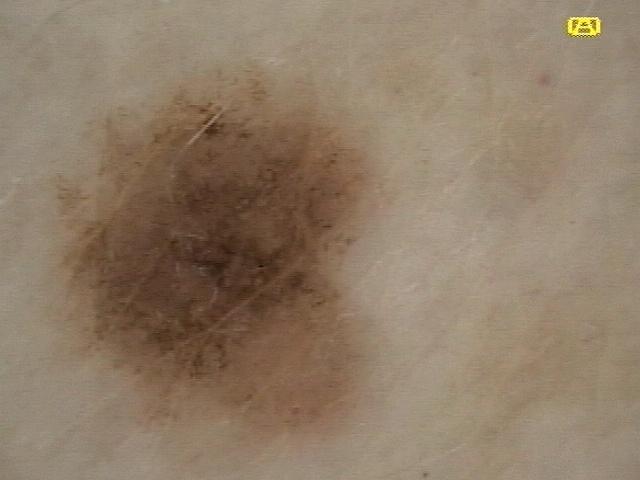A female subject in their mid-60s.
A skin lesion imaged with a dermatoscope.
The lesion involves an upper extremity.
Biopsy-confirmed as a nevus.